This image was taken at a distance; the affected area is the back of the hand and arm; the patient notes the lesion is fluid-filled, rough or flaky and raised or bumpy; the patient is male; the patient notes bothersome appearance, burning, darkening, itching, pain, enlargement and bleeding; no associated systemic symptoms reported:
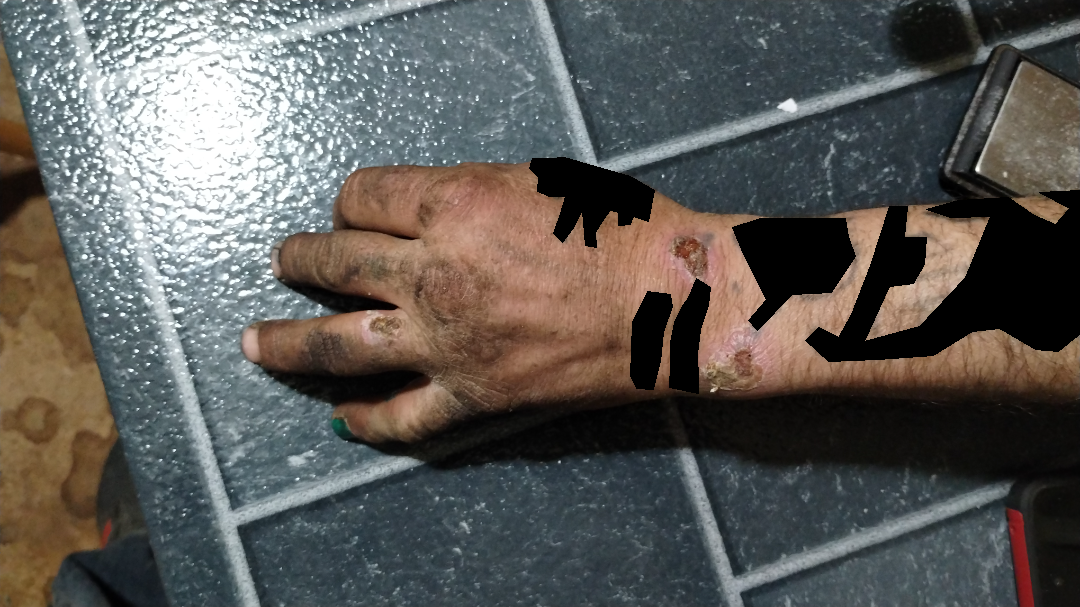{"assessment": "indeterminate"}